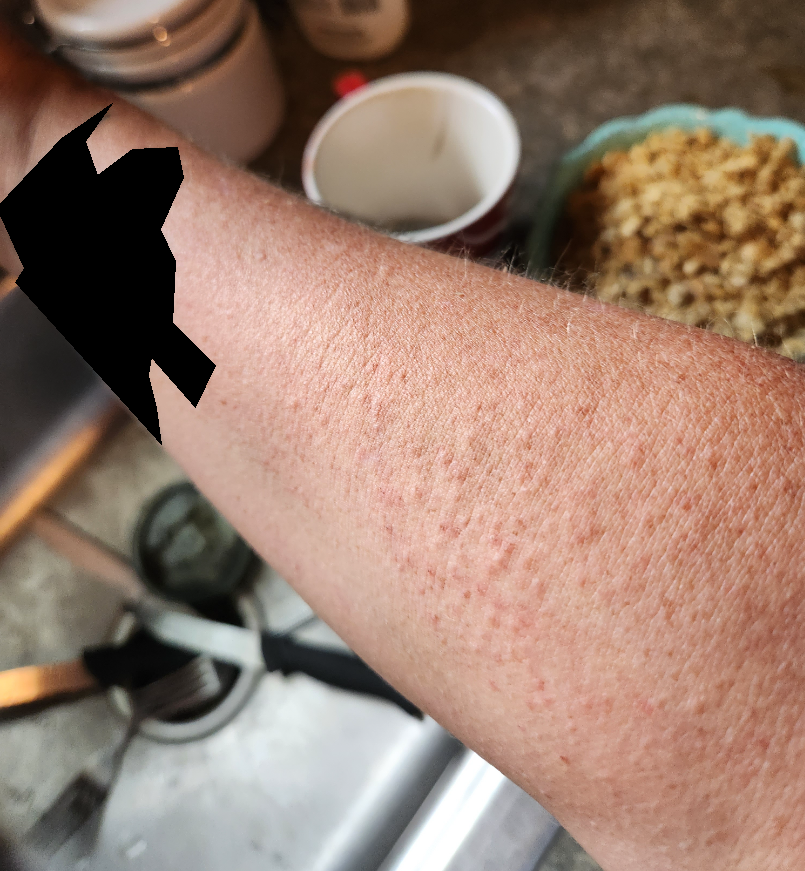Q: Could the case be diagnosed?
A: indeterminate
Q: Anatomic location?
A: leg and arm
Q: Image view?
A: at a distance
Q: Who is the patient?
A: female, age 40–49